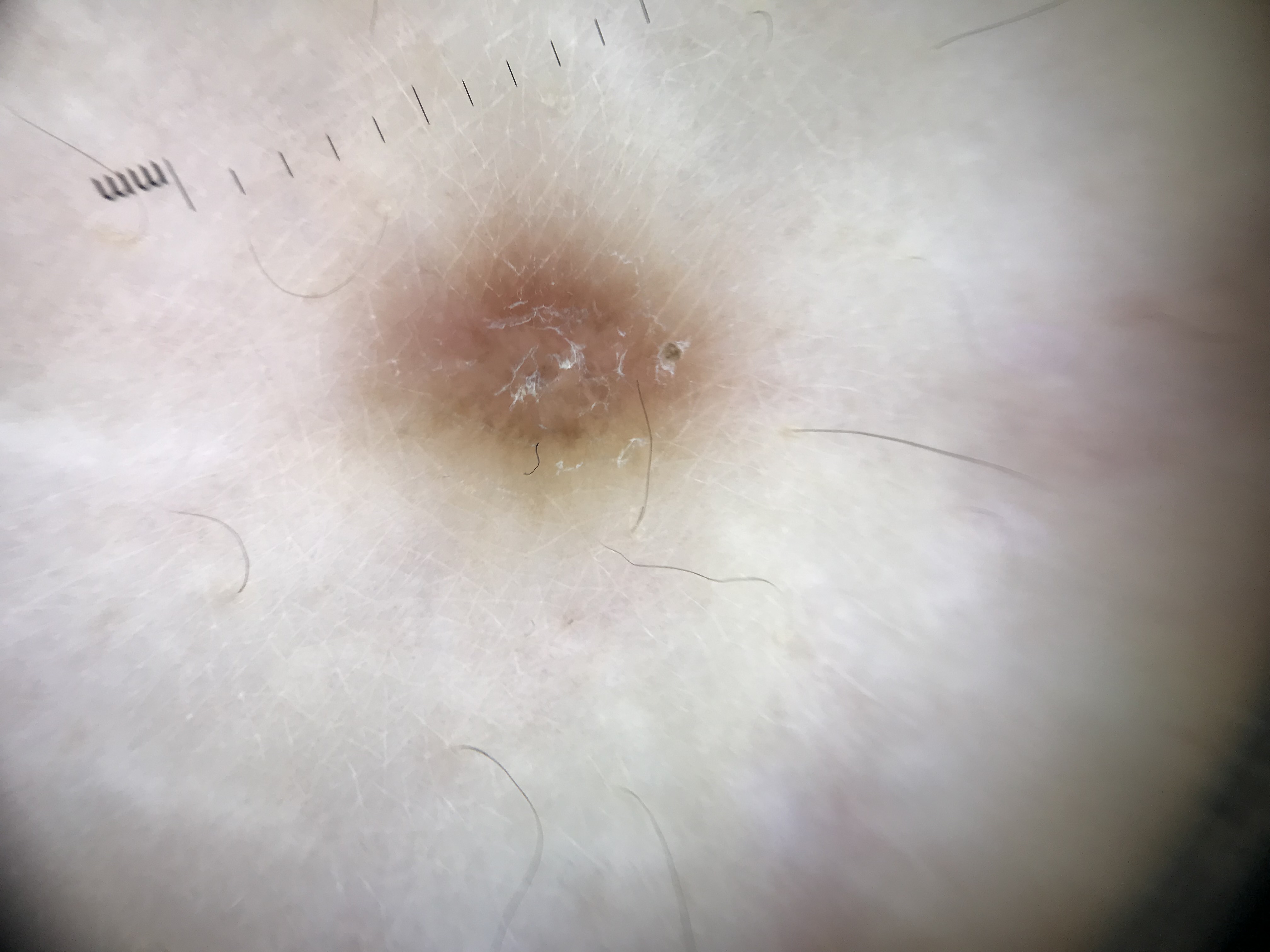Summary: A dermoscopy image of a single skin lesion. The morphology is that of a fibro-histiocytic lesion. Conclusion: Diagnosed as a benign lesion — a dermatofibroma.